A female subject 75 years old. By self-report, a personal history of cancer and a personal history of skin cancer. The patient says their skin tans without first burning. A skin lesion imaged with a dermatoscope. Imaged for a research study, with no referral diagnosis recorded. A moderate number of moles by the patient's own estimate: 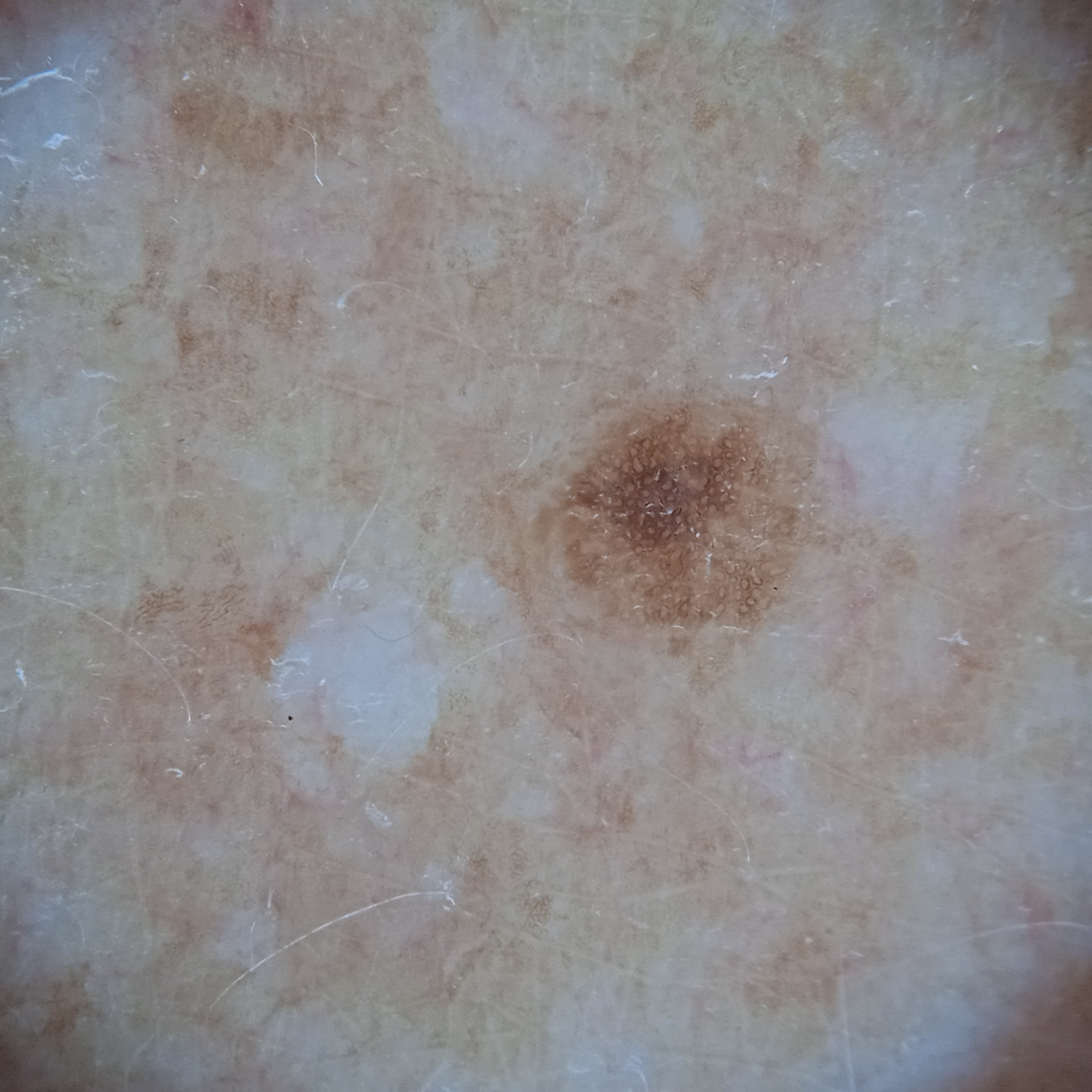Summary:
The lesion is about 2.7 mm across.
Impression:
The lesion was assessed as a melanocytic nevus.